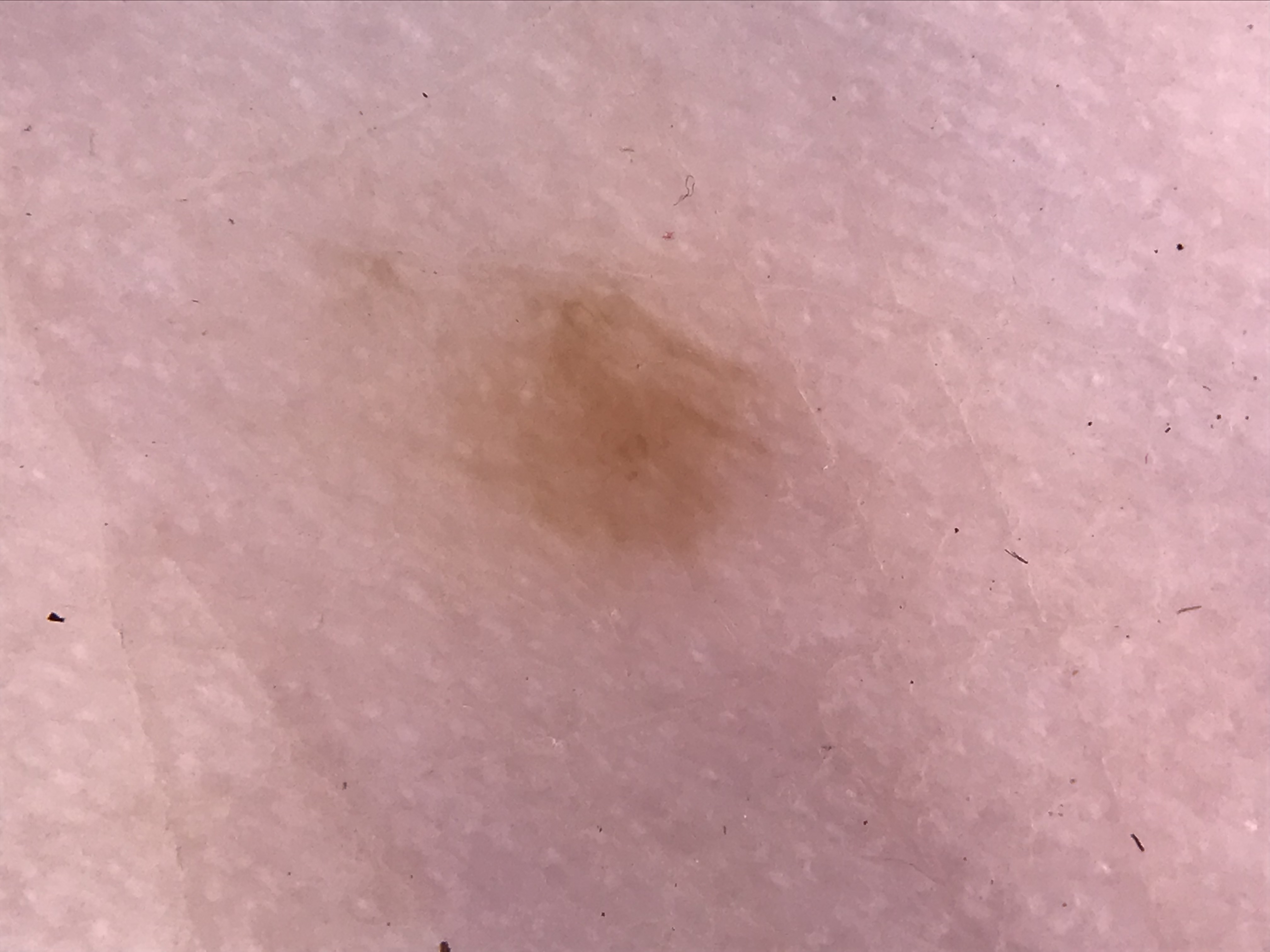Findings: A dermoscopic photograph of a skin lesion. Impression: Labeled as a banal lesion — an acral junctional nevus.